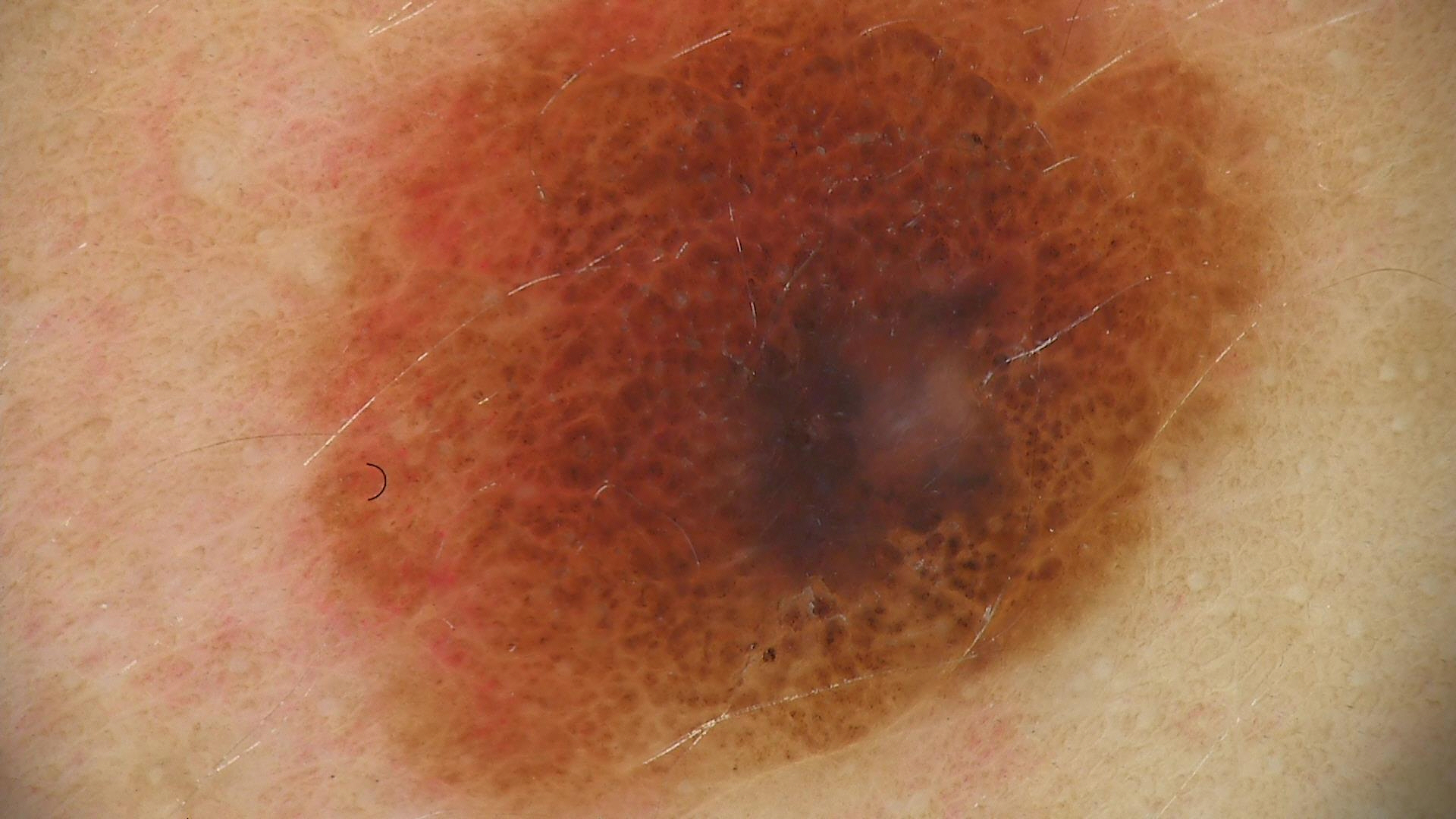assessment=dysplastic compound nevus (expert consensus).